Located on the front of the torso and head or neck, the contributor is female, the photo was captured at an angle.
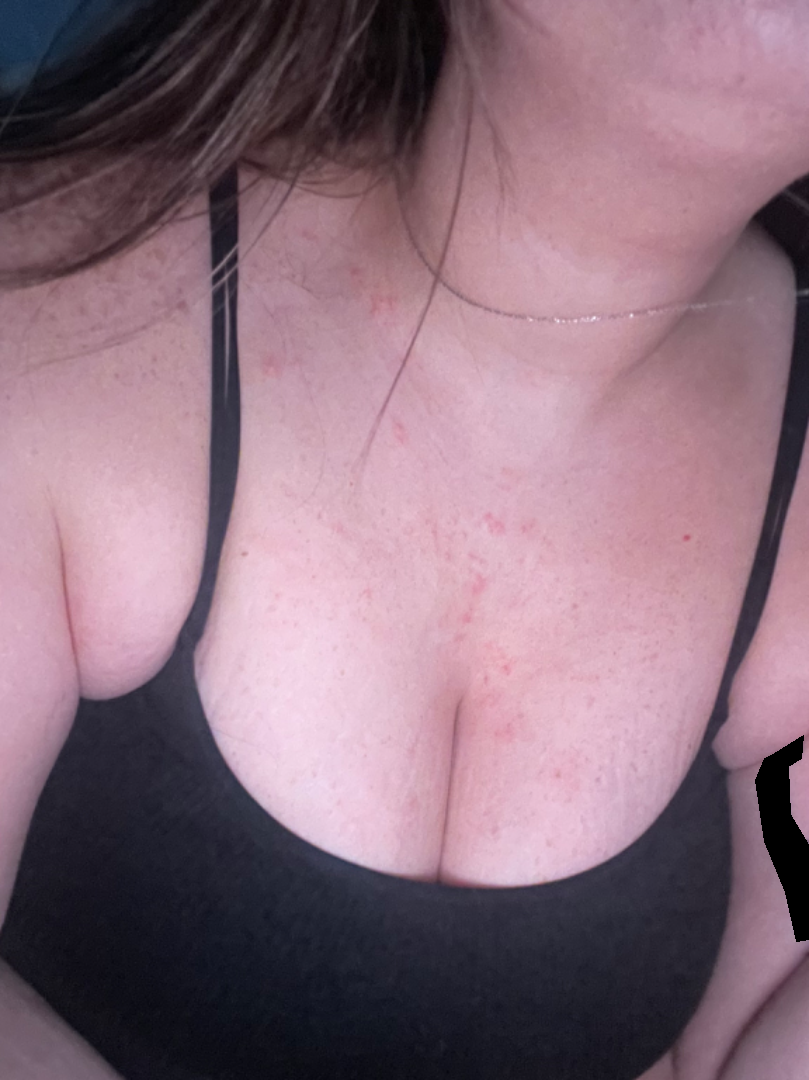• impression · most likely Folliculitis; also consider Acne; possibly Eczema